A dermoscopic close-up of a skin lesion.
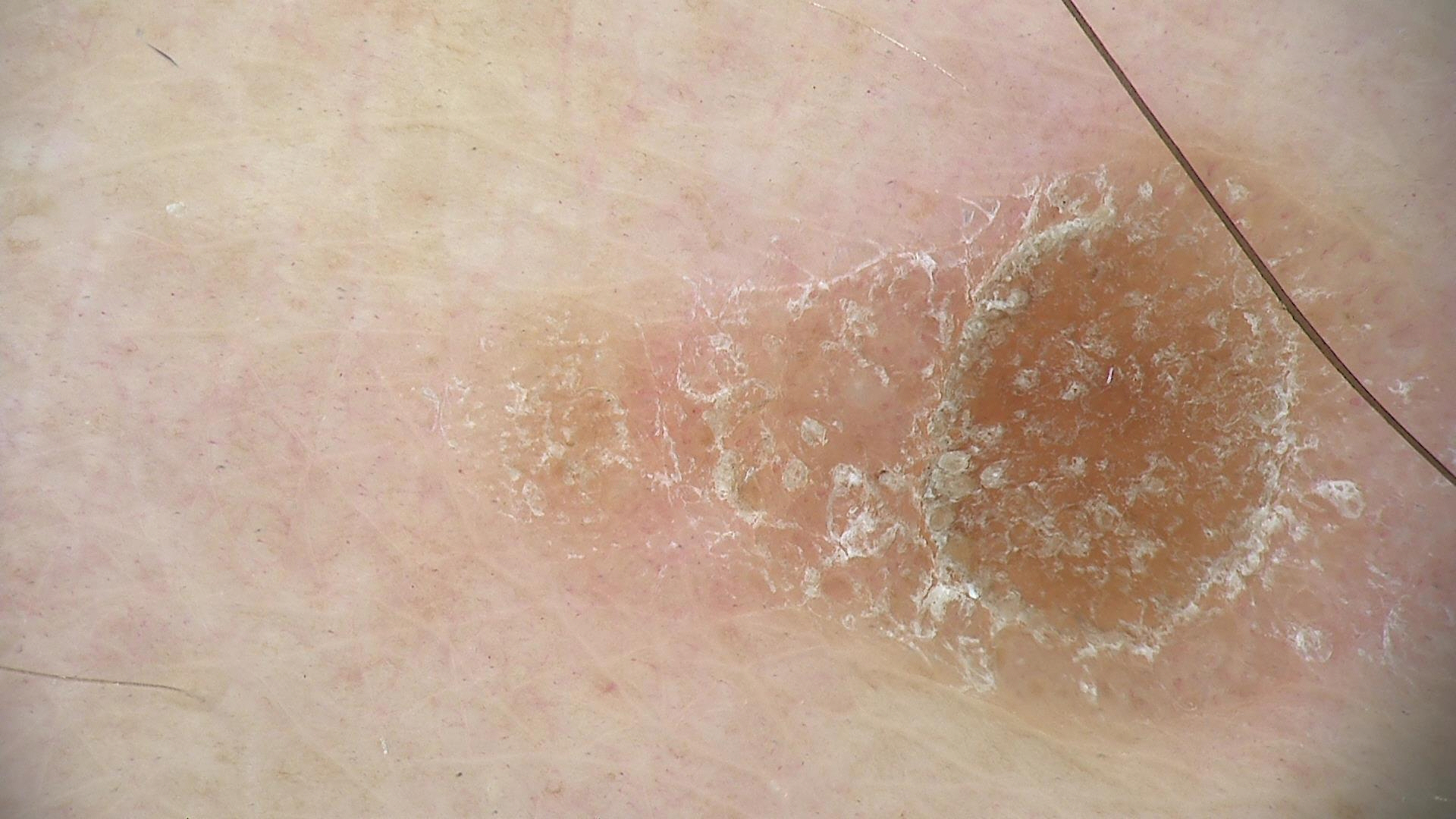Findings:
– diagnostic label: seborrheic keratosis (expert consensus)